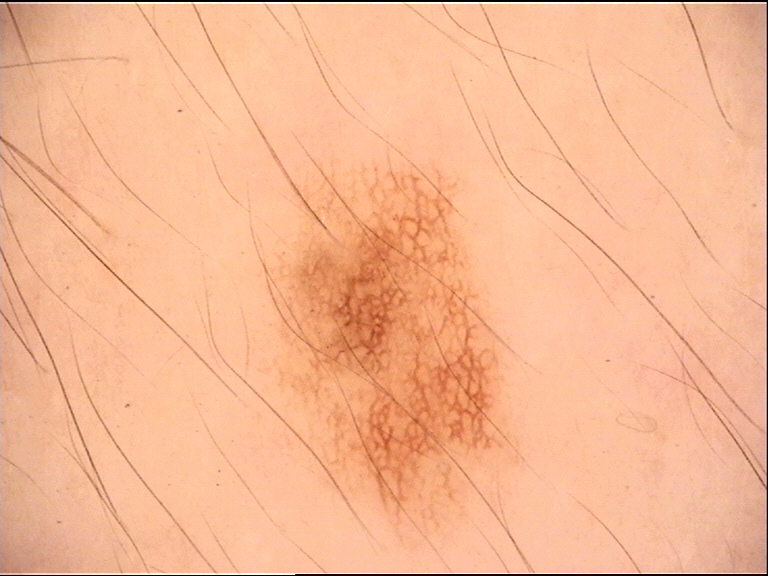Summary: The morphology is that of a banal lesion. Conclusion: Diagnosed as a junctional nevus.